A clinical photograph showing a skin lesion. The referring clinician suspected melanocytic nevus. On a questionnaire the patient reported a personal history of cancer and a family history of skin cancer. The patient says their skin tans without first burning. A female subject 64 years old: 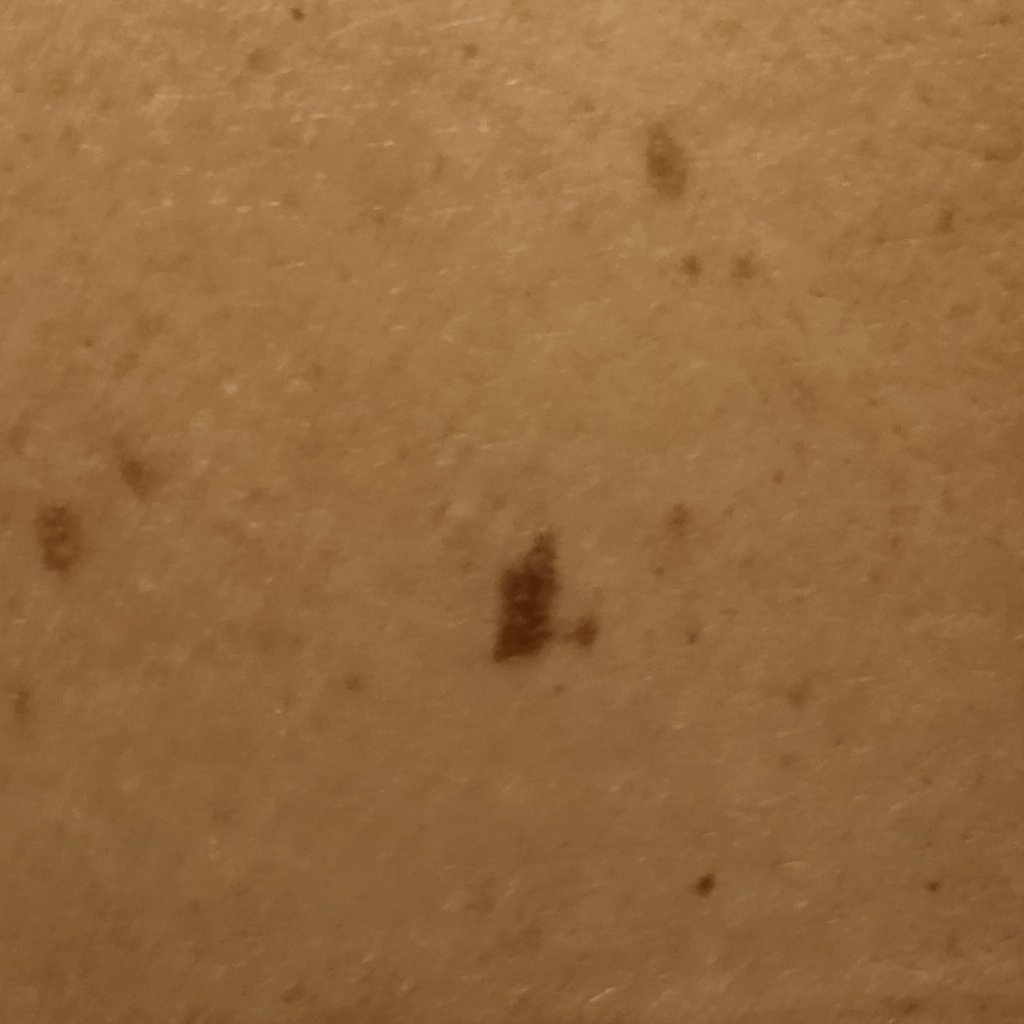Clinical context: Located on the back. The lesion is about 8.3 mm across. Conclusion: Histopathologically confirmed as an atypical (dysplastic) nevus, following excision.